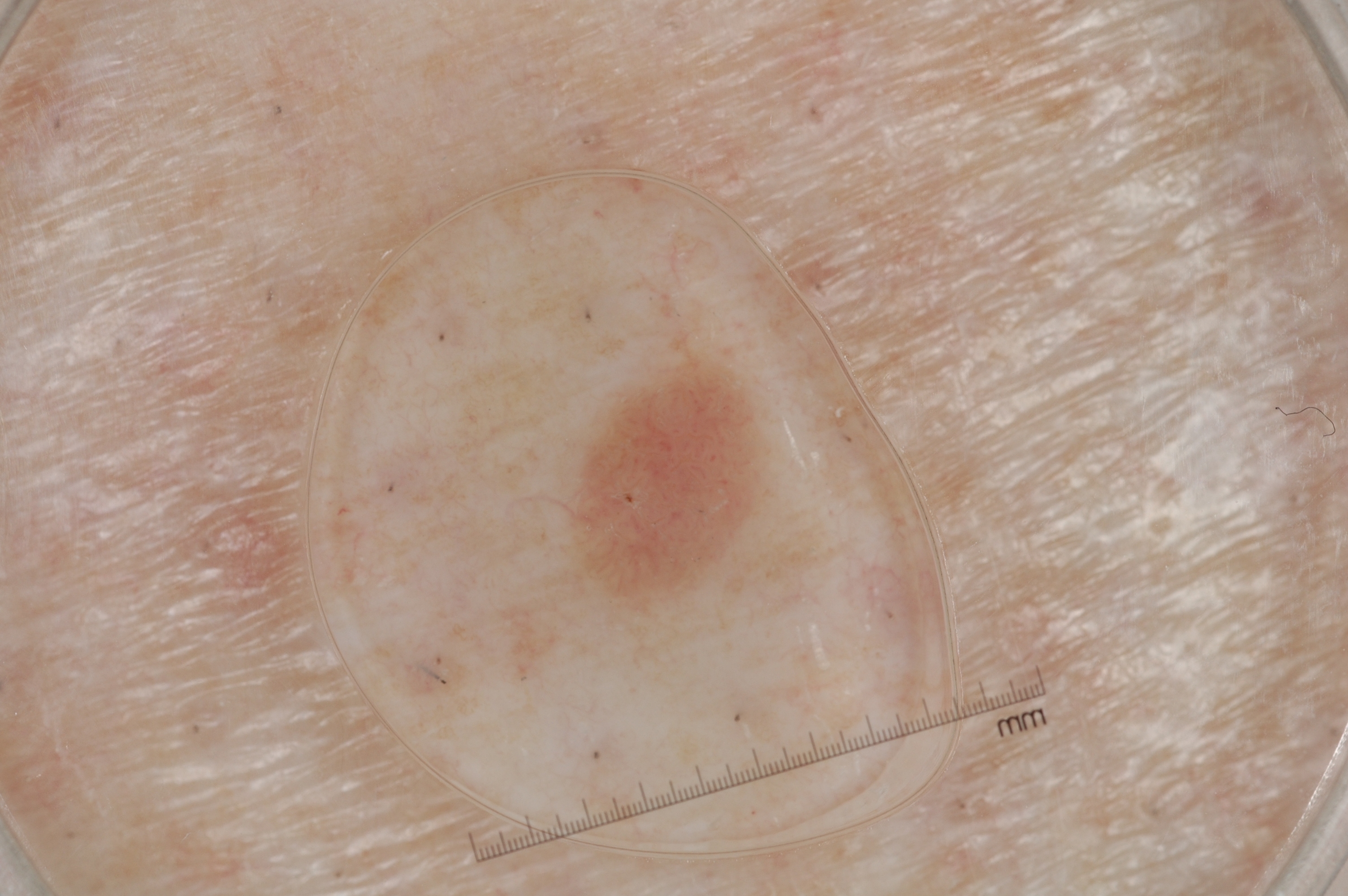  patient:
    sex: female
    age_approx: 55
  image:
    modality: dermoscopy
  lesion_location:
    bbox_xyxy:
      - 567
      - 362
      - 769
      - 619
  dermoscopic_features:
    present: []
    absent:
      - streaks
      - negative network
      - milia-like cysts
      - pigment network
  diagnosis:
    name: seborrheic keratosis
    malignancy: benign
    lineage: keratinocytic
    provenance: clinical